This is a close-up image. The back of the hand, arm and head or neck are involved. Female contributor, age 30–39.
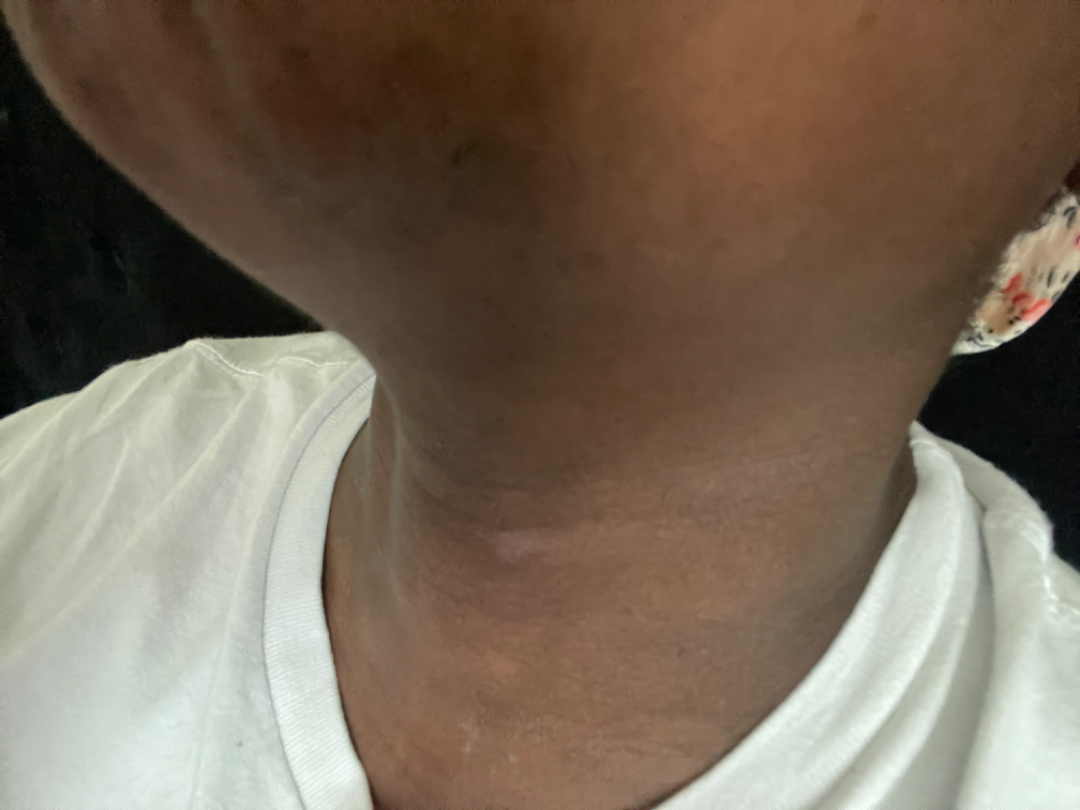The case was difficult to assess from the available photograph. The condition has been present for three to twelve months. The lesion is described as raised or bumpy and rough or flaky. The patient reported no systemic symptoms.